A skin lesion imaged with a dermatoscope.
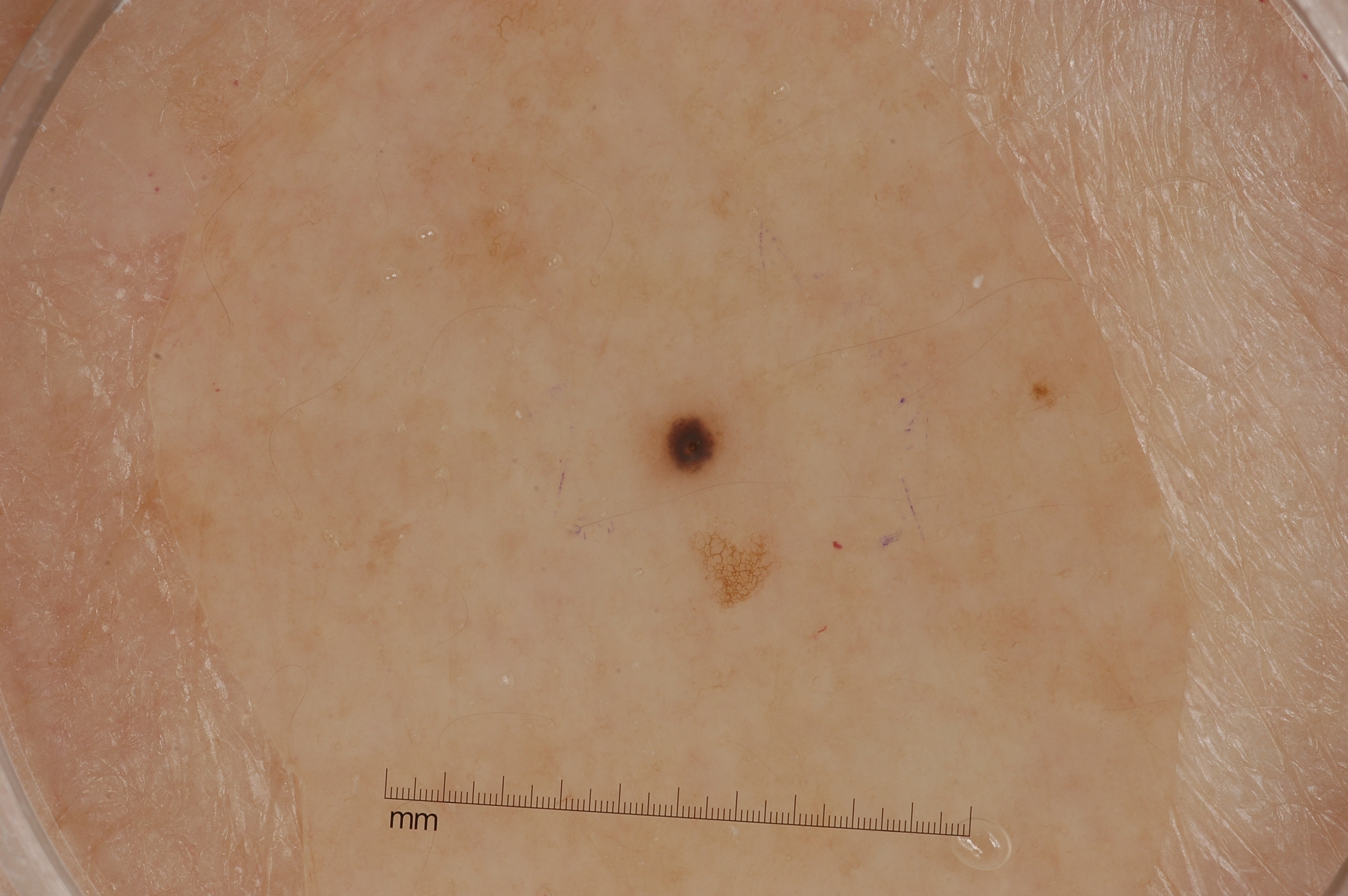absent dermoscopic features — pigment network, streaks, milia-like cysts, and negative network
bounding box — x1=649 y1=408 x2=726 y2=481
impression — a melanocytic nevus